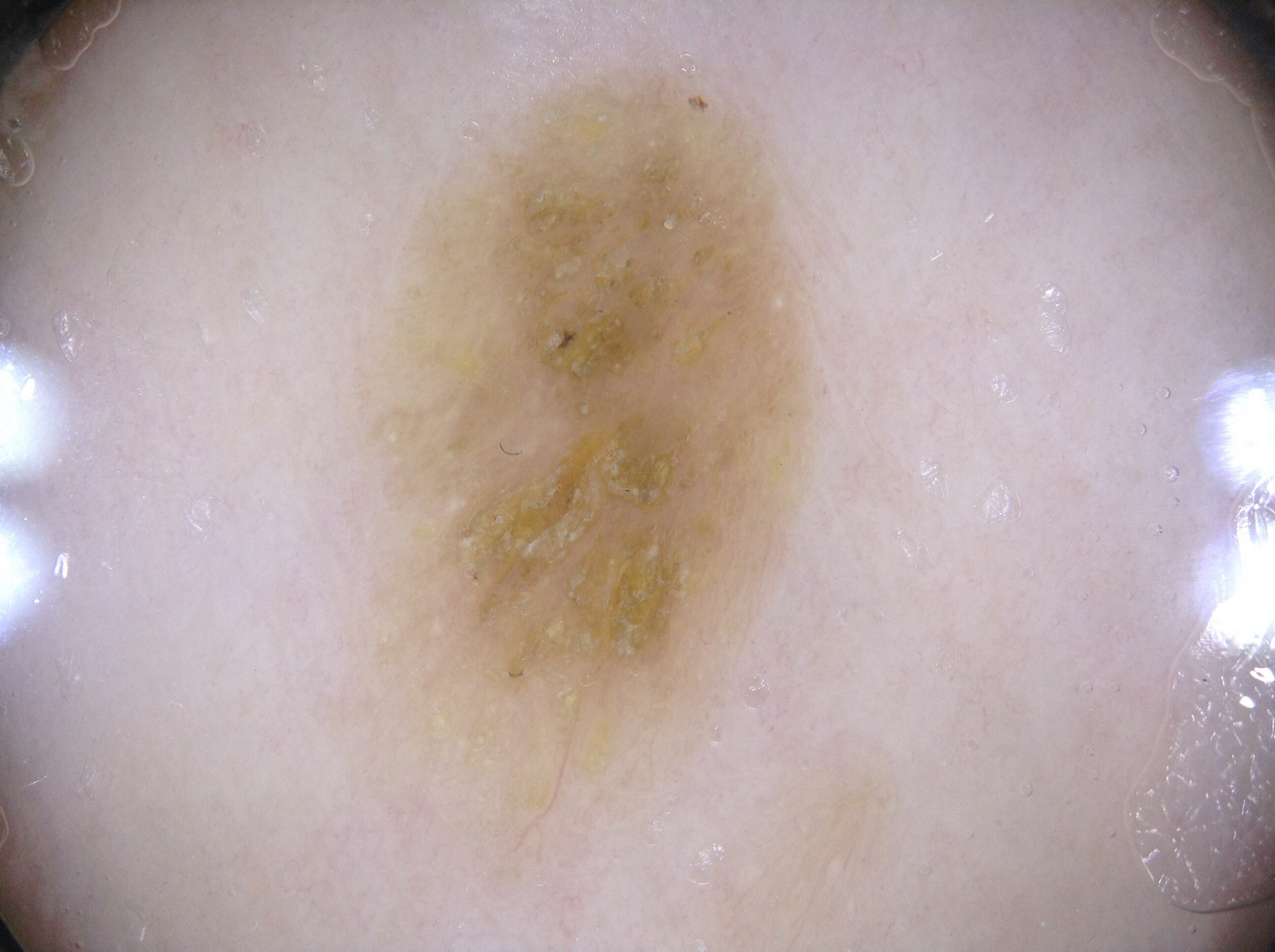image: dermoscopy of a skin lesion
subject: female, aged around 60
lesion size: moderate
dermoscopic findings: milia-like cysts
bounding box: bbox=[356, 48, 821, 883]
diagnosis: a seborrheic keratosis